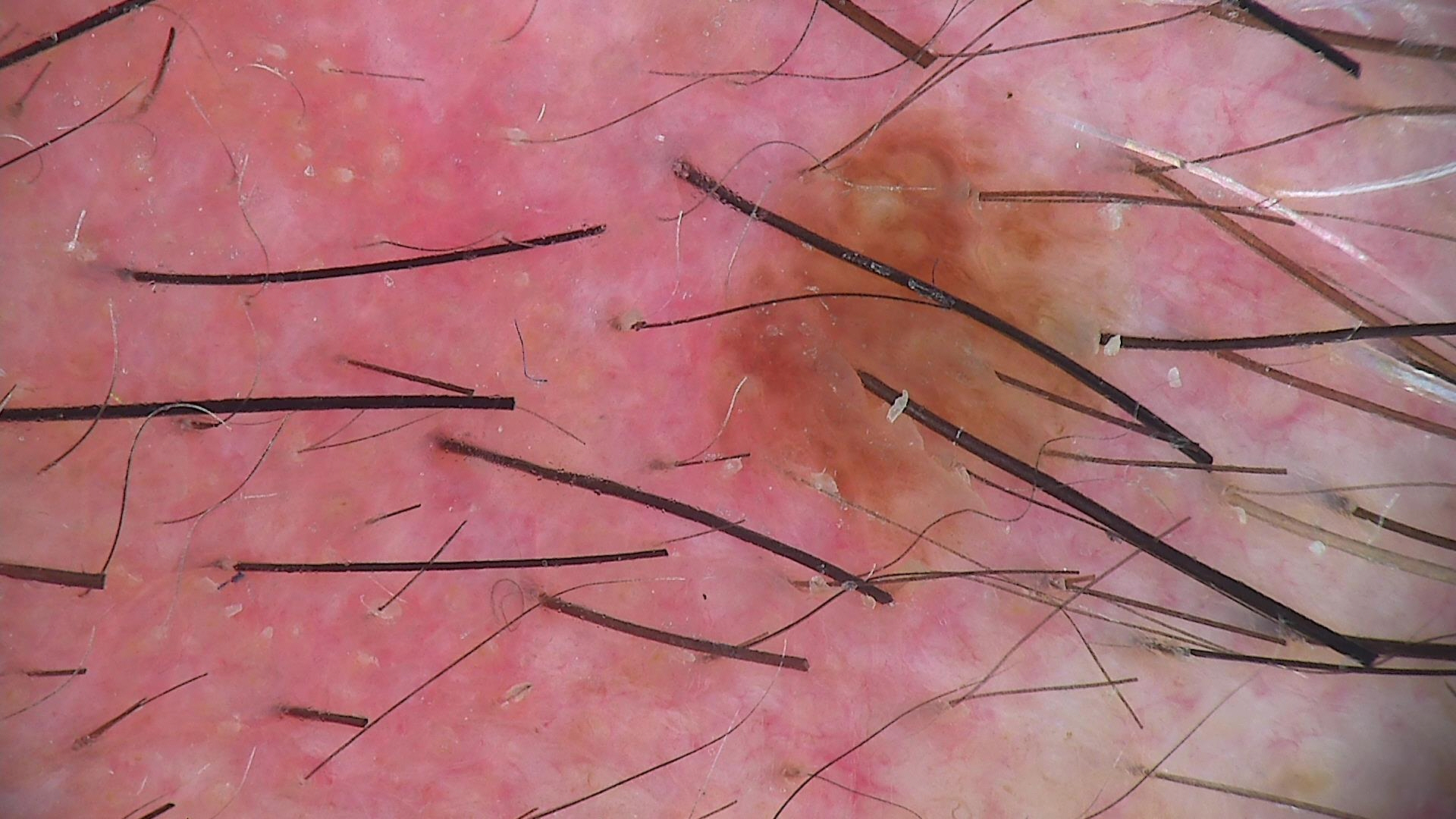The diagnosis was a keratinocytic lesion — a seborrheic keratosis.